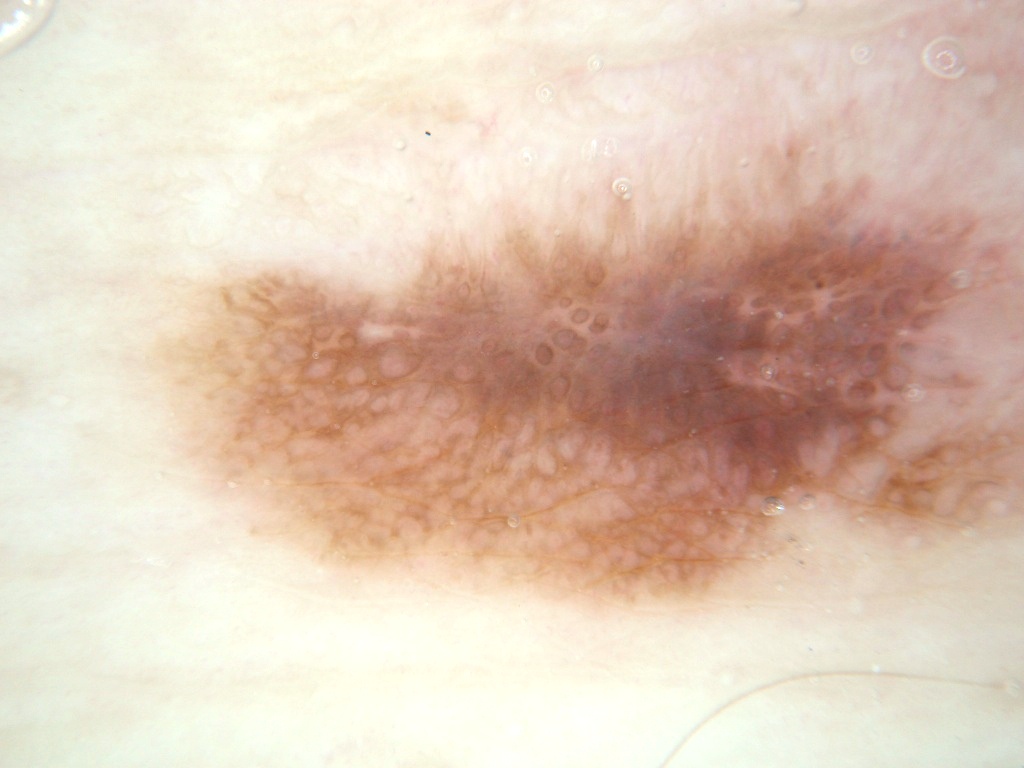This is a dermoscopic photograph of a skin lesion.
A male subject aged approximately 40.
The visible lesion spans box(131, 65, 1018, 658).
Dermoscopy demonstrates negative network and pigment network.
The diagnostic assessment was a melanocytic nevus, a benign skin lesion.